A dermoscopic image of a skin lesion: 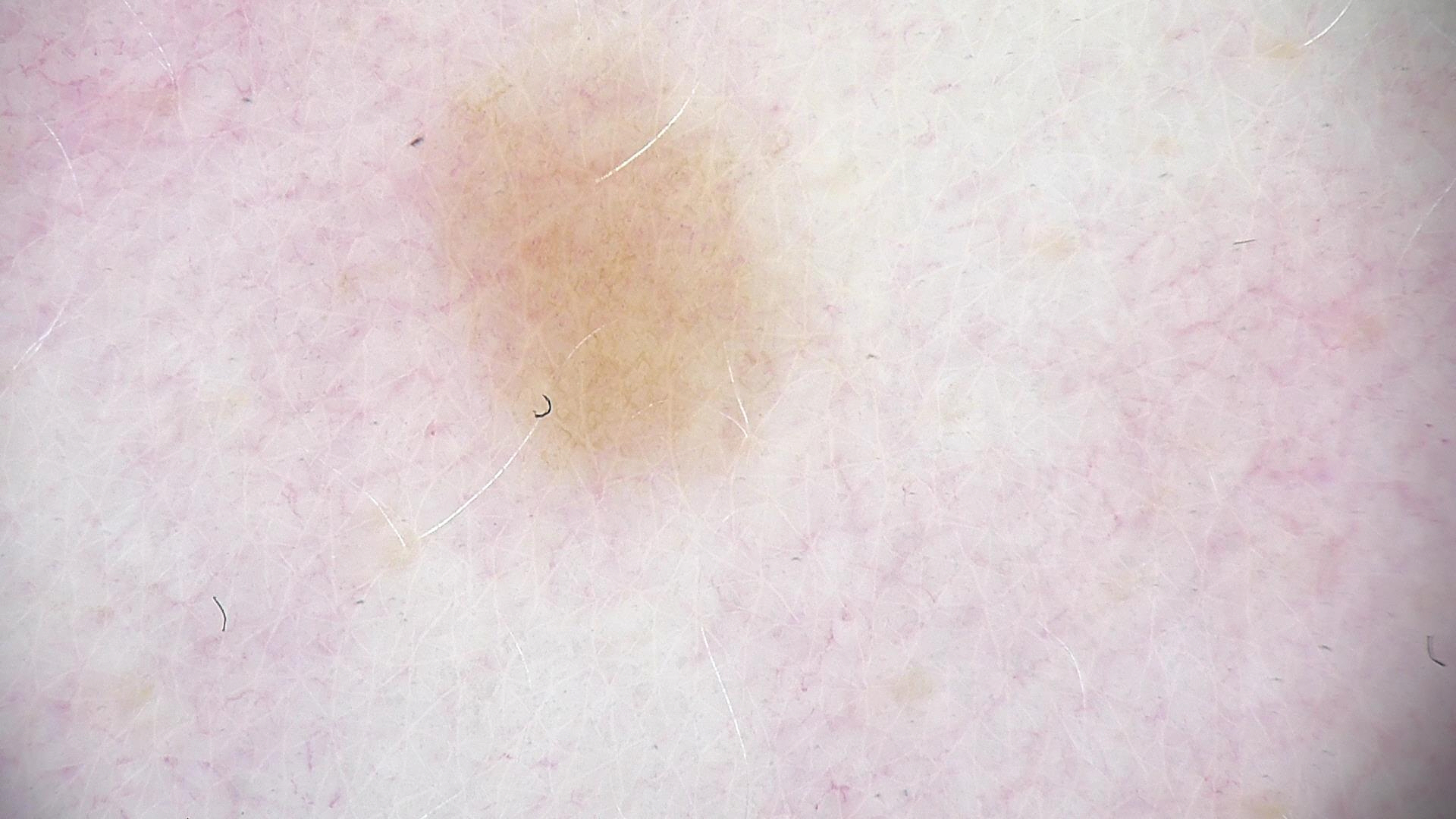Diagnosed as a benign lesion — a dysplastic junctional nevus.